A dermoscopy image of a single skin lesion.
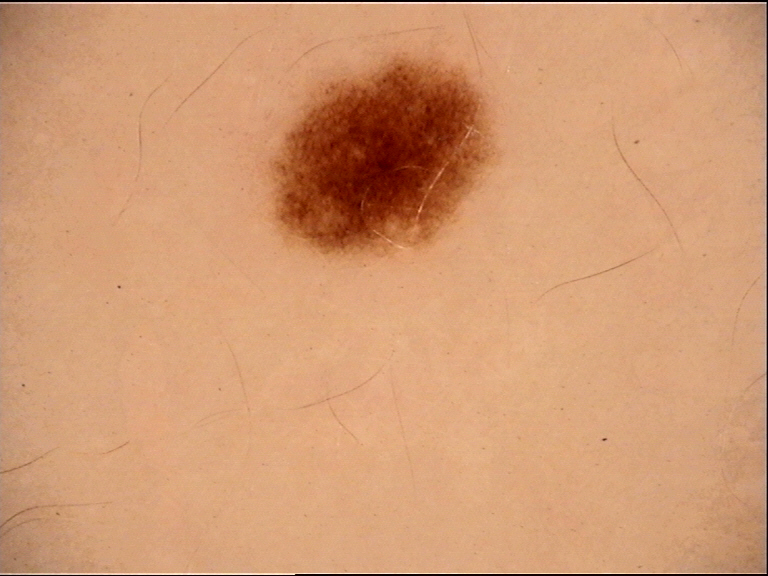Diagnosed as a dysplastic junctional nevus.